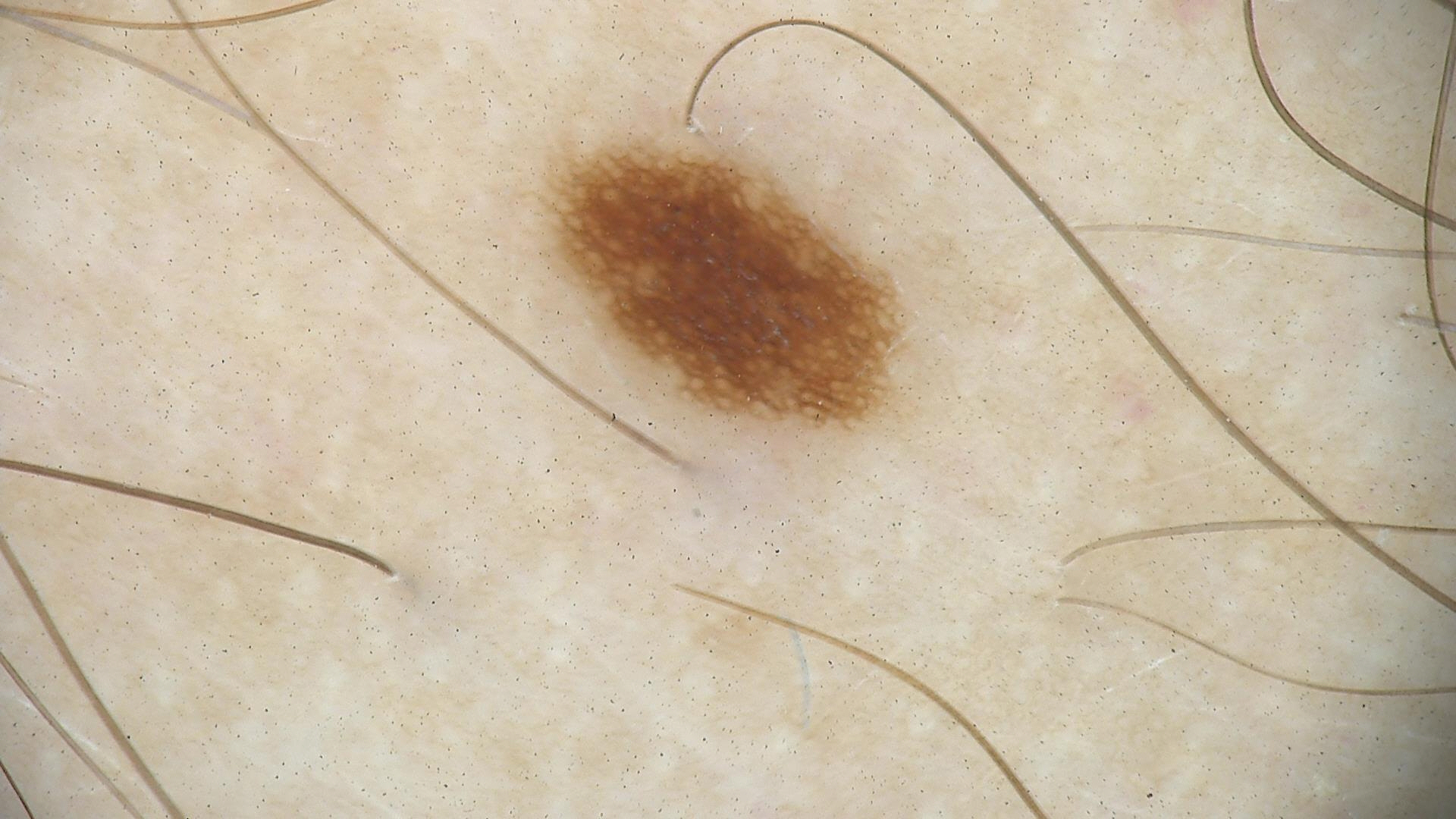| feature | finding |
|---|---|
| imaging | dermatoscopy |
| diagnosis | dysplastic junctional nevus (expert consensus) |